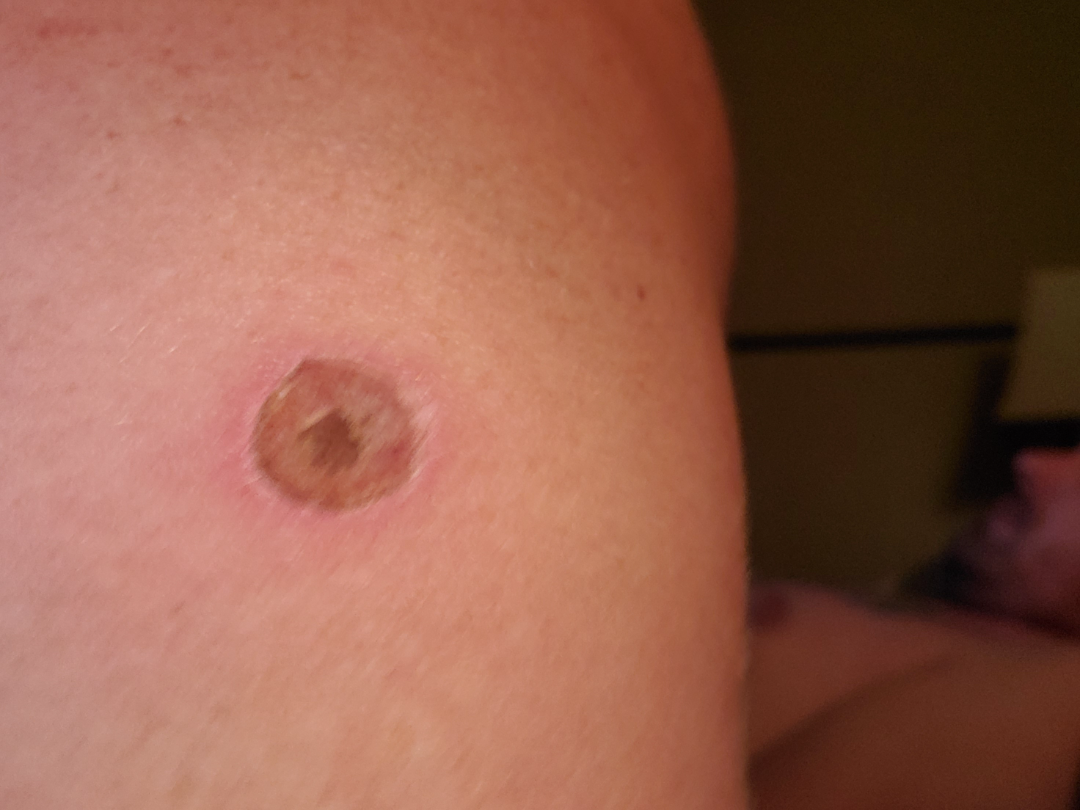The contributor is 40–49, female. No associated lesion symptoms were reported. No relevant systemic symptoms. Located on the arm. This is a close-up image. The contributor notes the condition has been present for less than one week. On dermatologist assessment of the image: Ecthyma (54%); Chronic ulcer of skin (23%); Skin lesion in drug addict (23%).